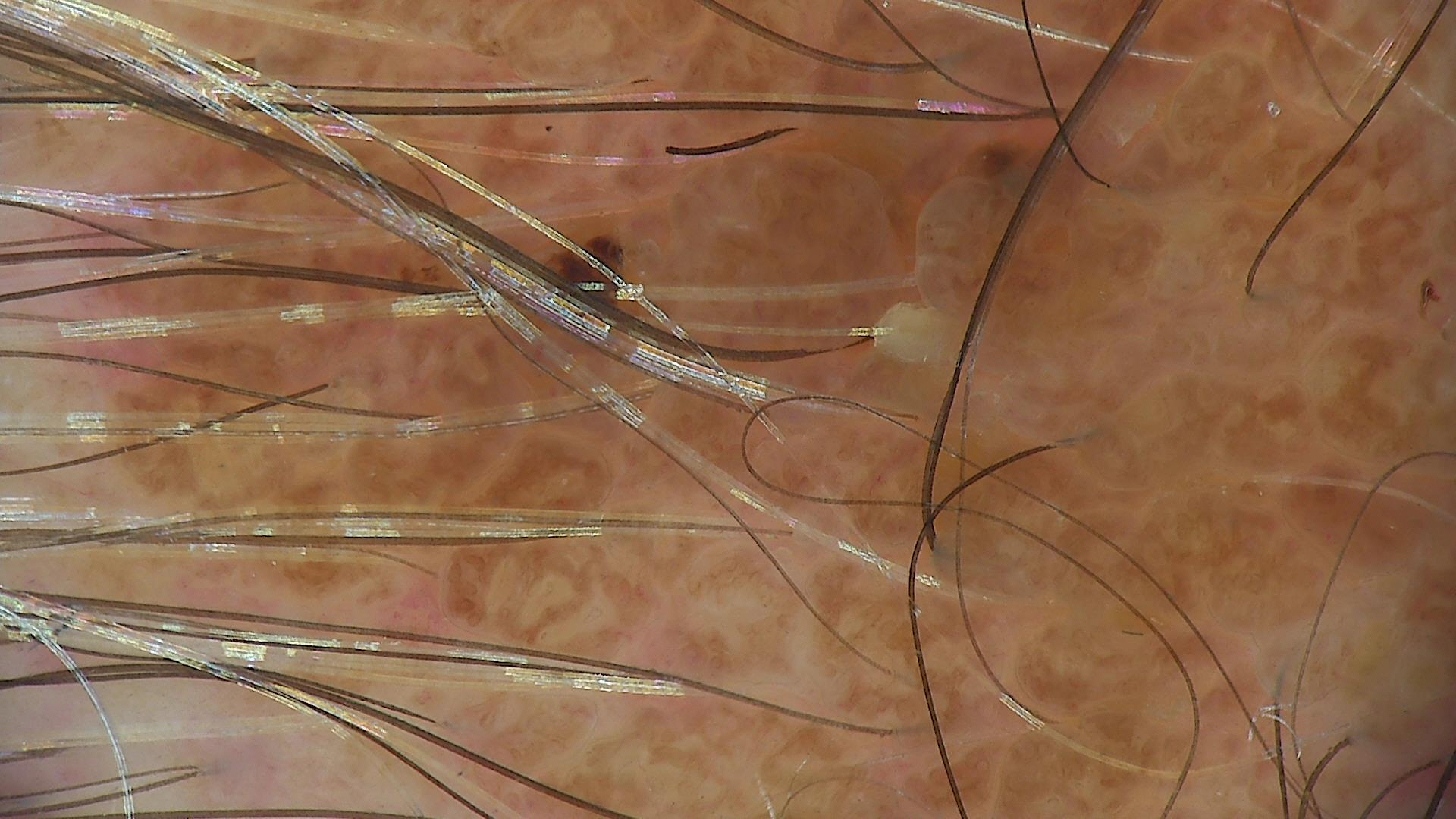A skin lesion imaged with a dermatoscope.
The architecture is that of a keratinocytic lesion.
The diagnosis was a benign lesion — a seborrheic keratosis.